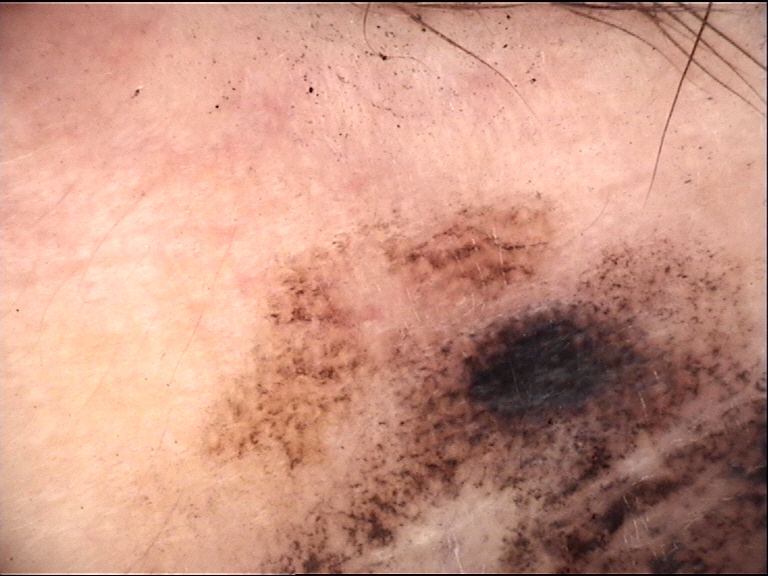class: lentigo maligna (biopsy-proven).